A male patient roughly 70 years of age — 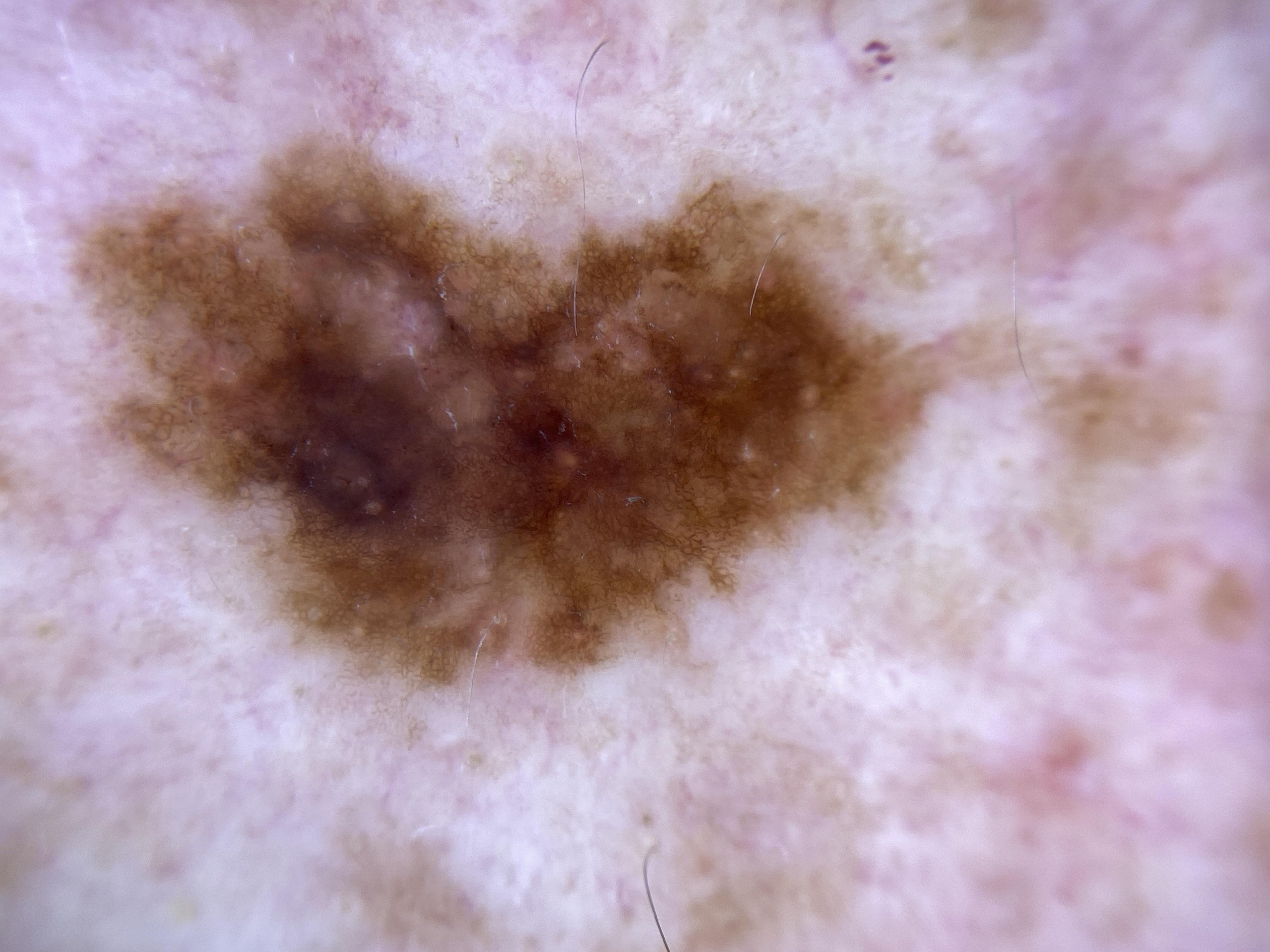site = the trunk, diagnosis = Nevus (biopsy-proven).